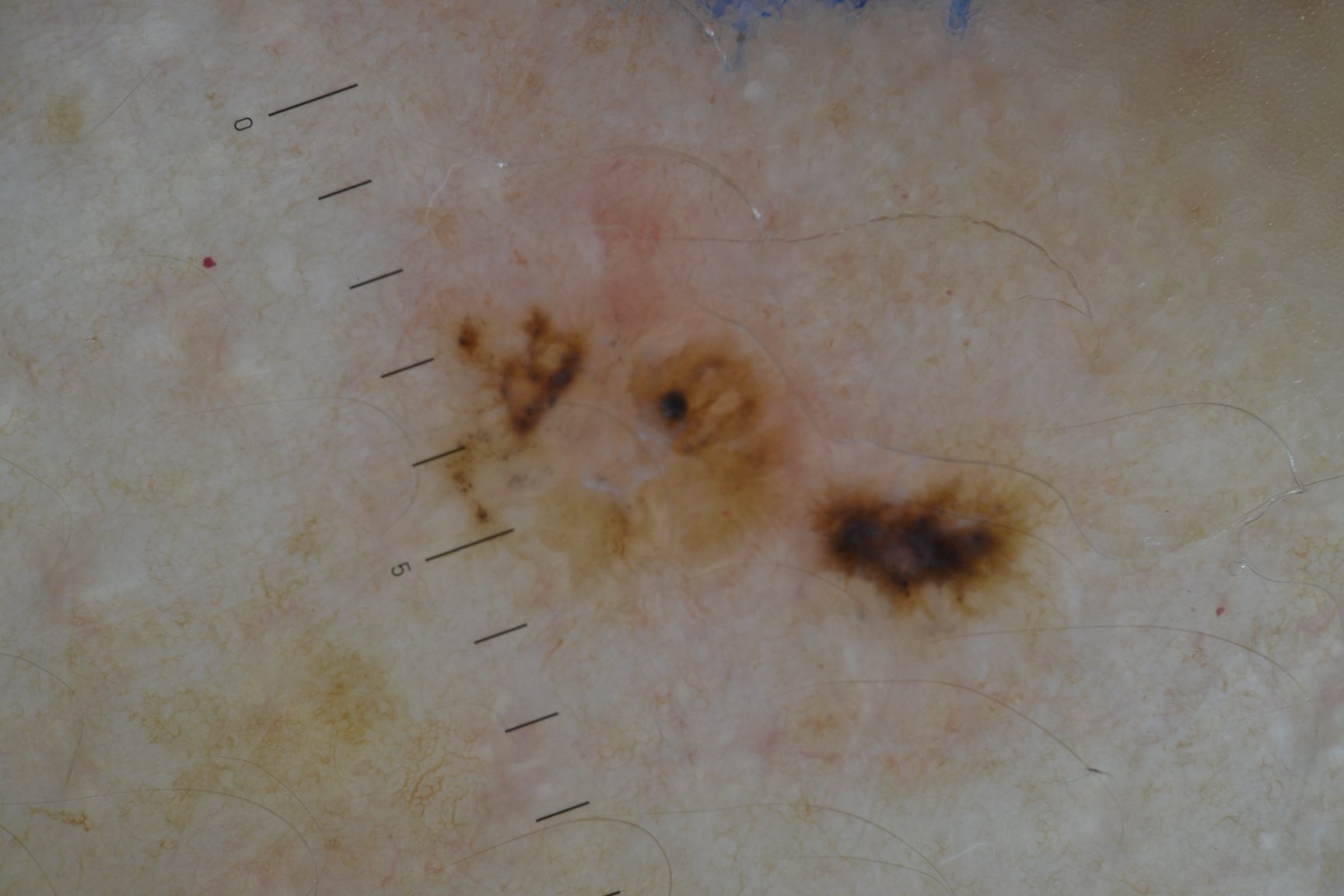{
  "diagnosis": {
    "name": "basal cell carcinoma",
    "code": "bcc",
    "malignancy": "malignant",
    "super_class": "non-melanocytic",
    "confirmation": "histopathology"
  }
}